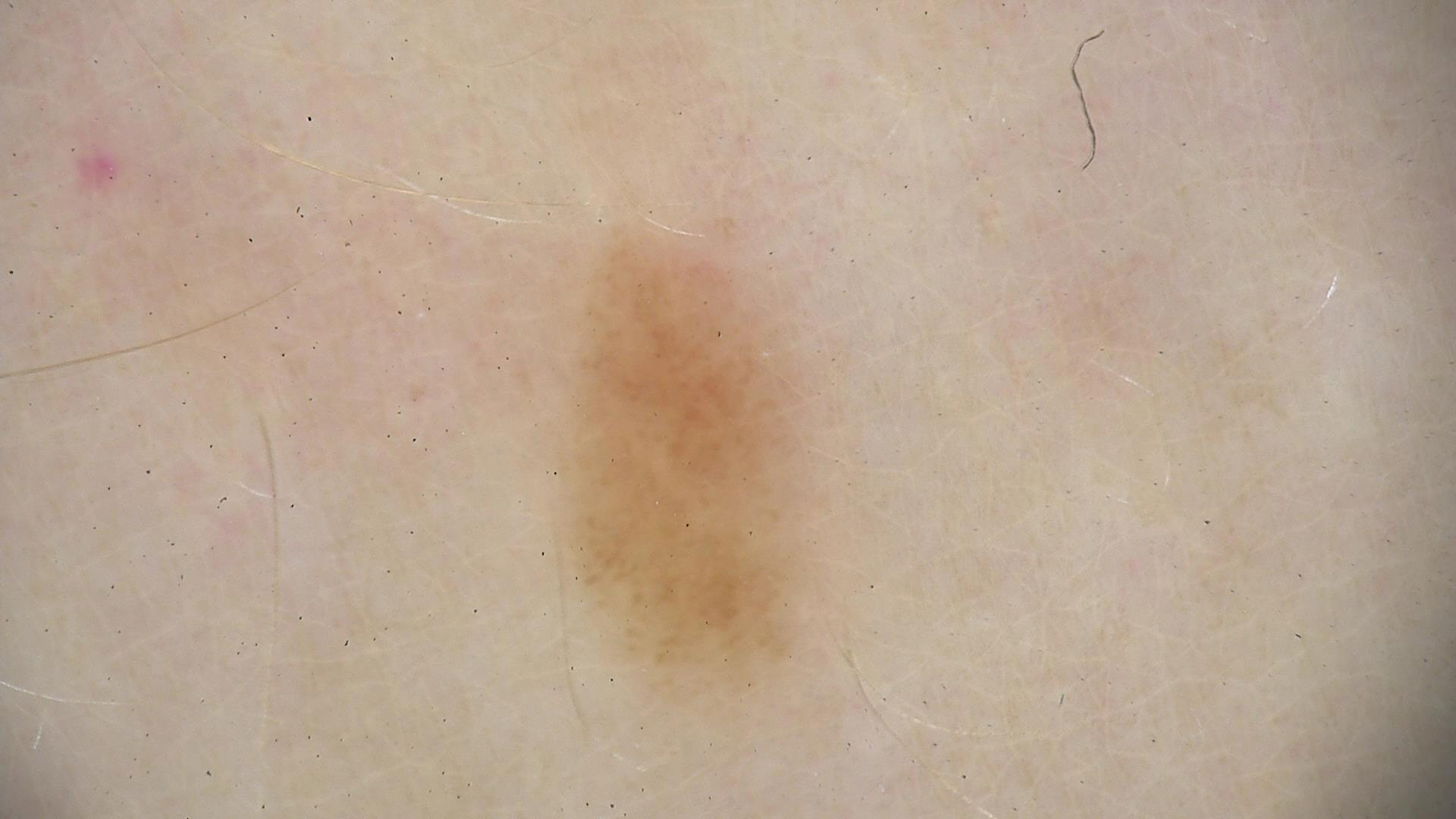Conclusion: The diagnosis was a junctional nevus.